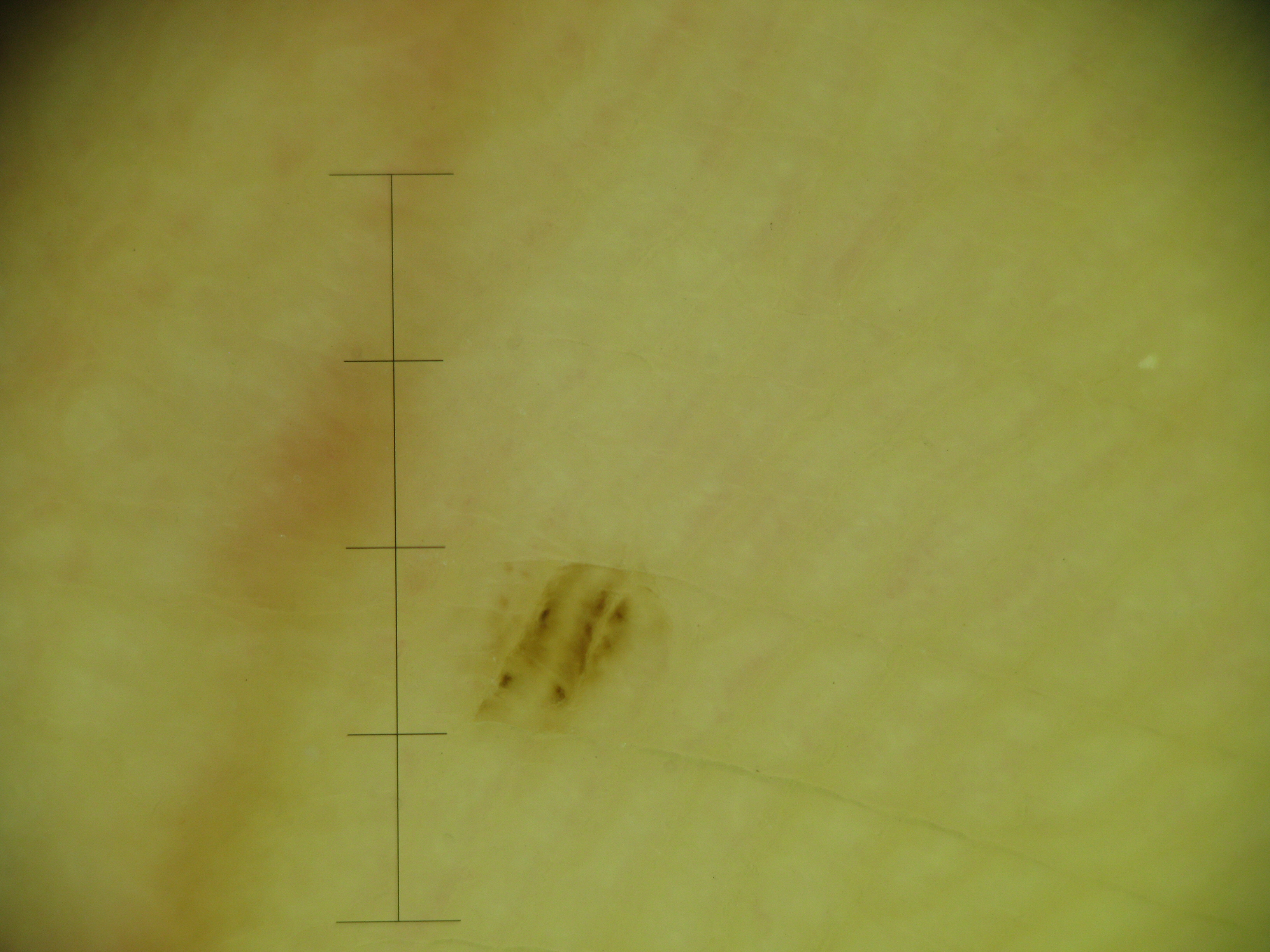A dermoscopic photograph of a skin lesion.
The diagnosis was a banal lesion — an acral junctional nevus.